Contact-polarized dermoscopy of a skin lesion — 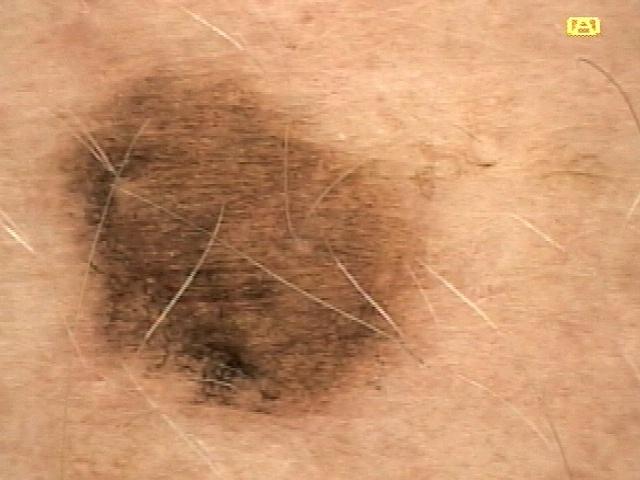pathology = Nevus (biopsy-proven).